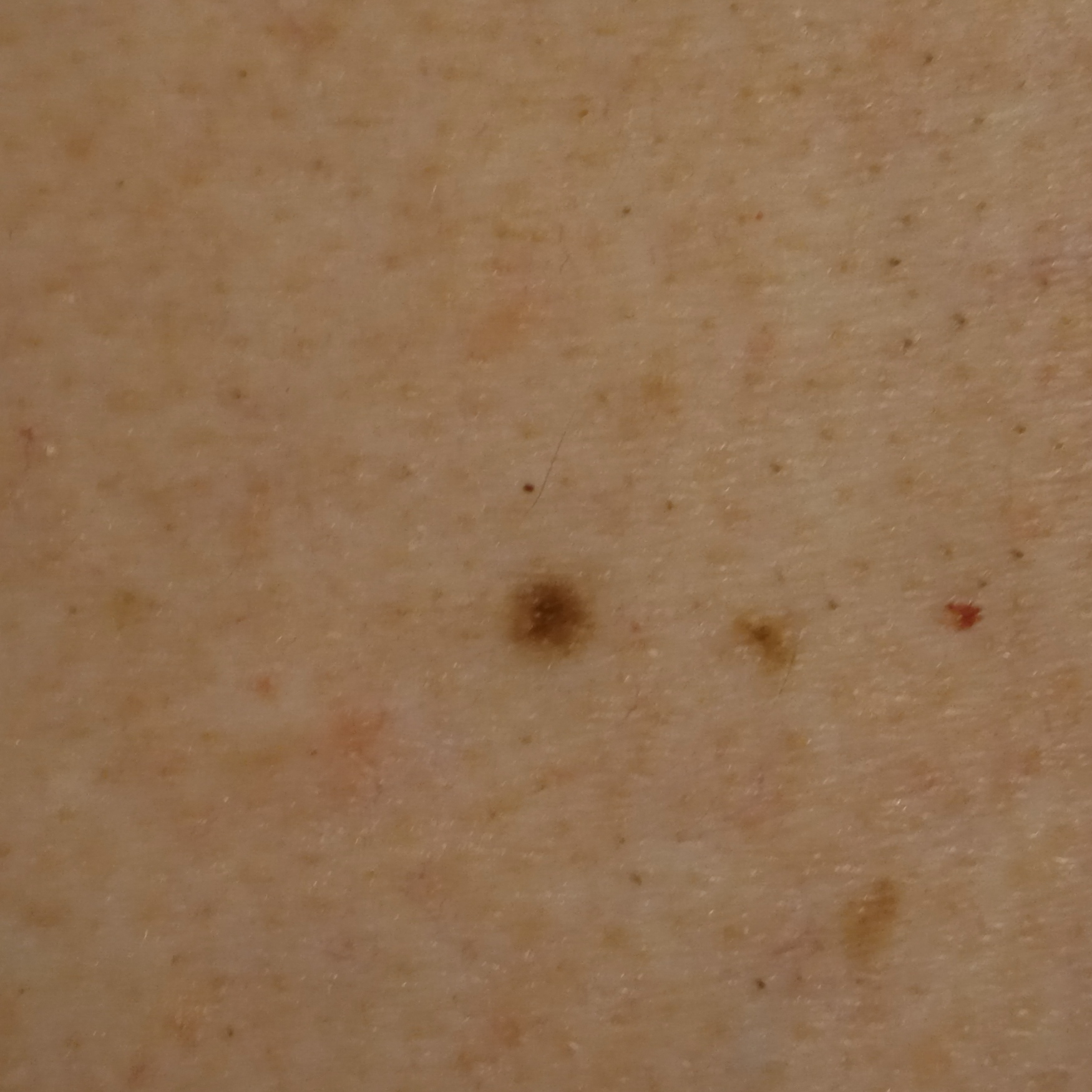{
  "image": "clinical photo",
  "referral": "research study (no referral diagnosis)",
  "patient": {
    "age": 65,
    "sex": "male"
  },
  "lesion_location": "the back",
  "lesion_size": {
    "diameter_mm": 3.6
  },
  "diagnosis": {
    "name": "melanocytic nevus",
    "malignancy": "benign"
  }
}